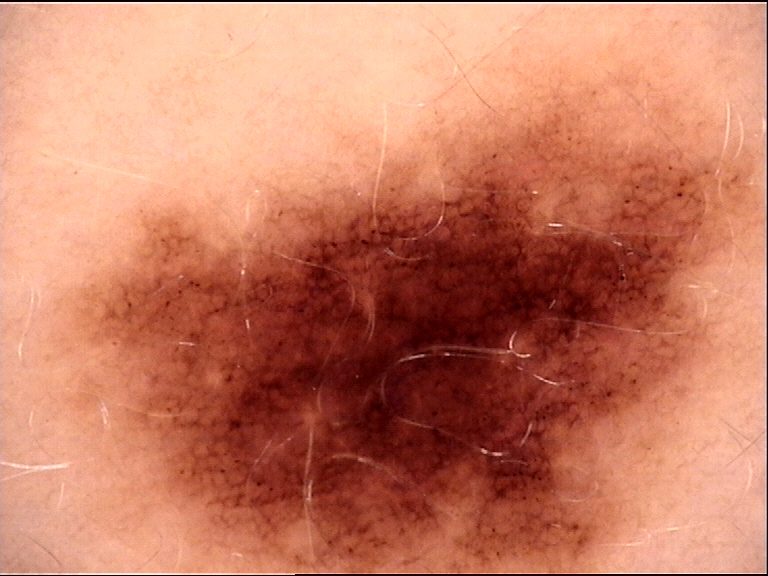imaging: dermatoscopy
class: dysplastic junctional nevus (expert consensus)